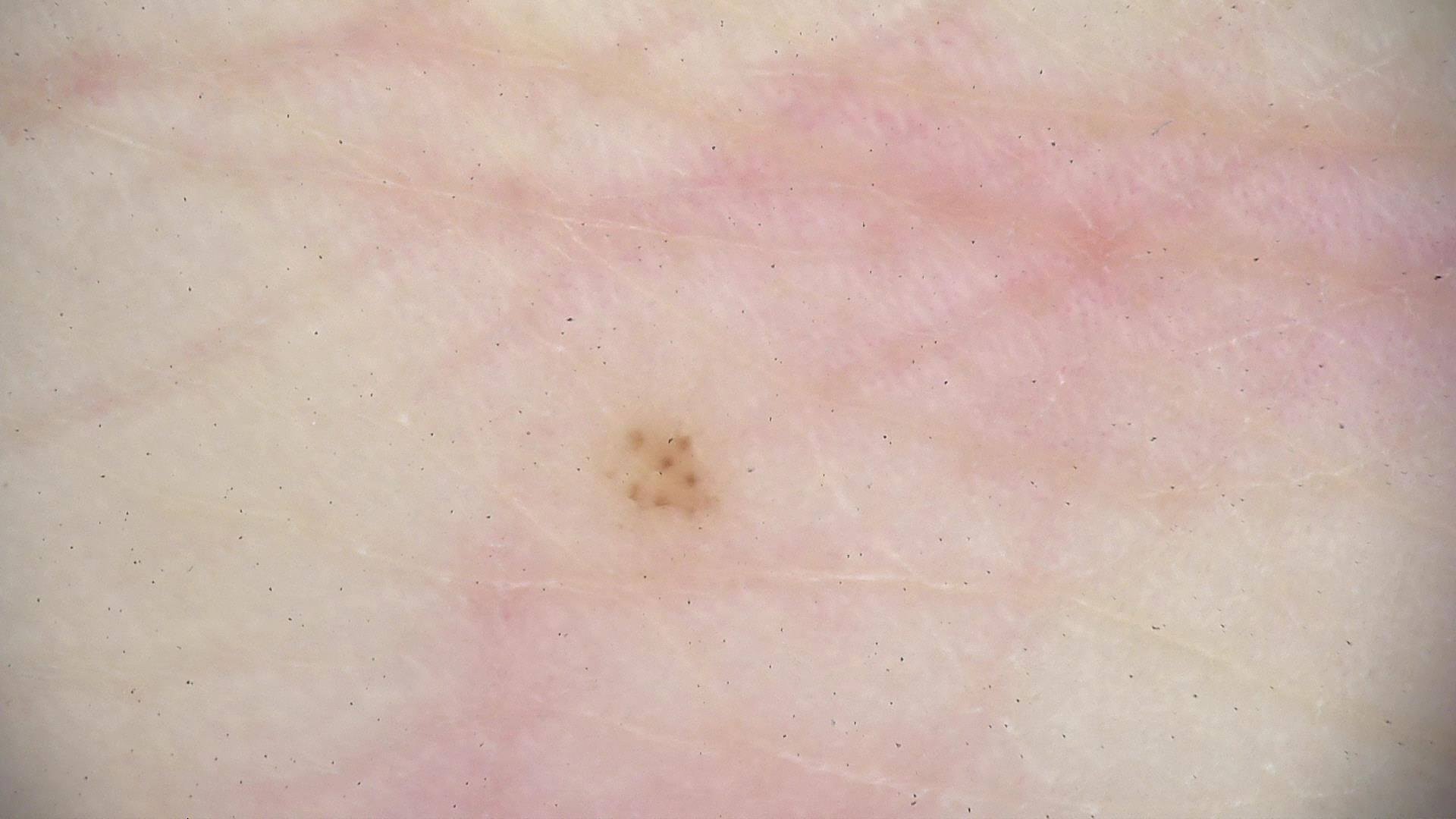<case>
<image>dermoscopy</image>
<diagnosis>
<name>acral dysplastic junctional nevus</name>
<code>ajd</code>
<malignancy>benign</malignancy>
<super_class>melanocytic</super_class>
<confirmation>expert consensus</confirmation>
</diagnosis>
</case>